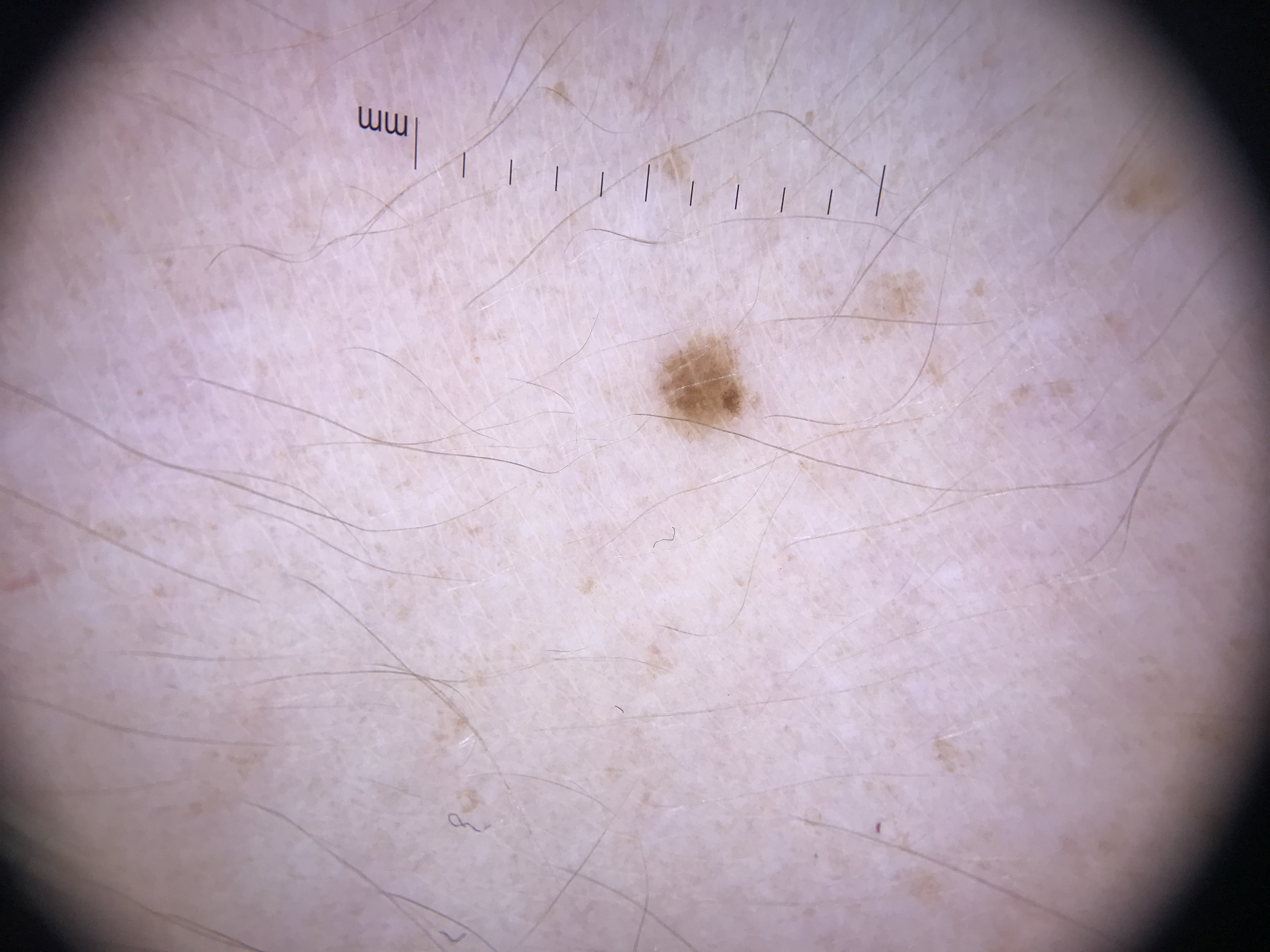The diagnostic label was a benign lesion — a dysplastic junctional nevus.